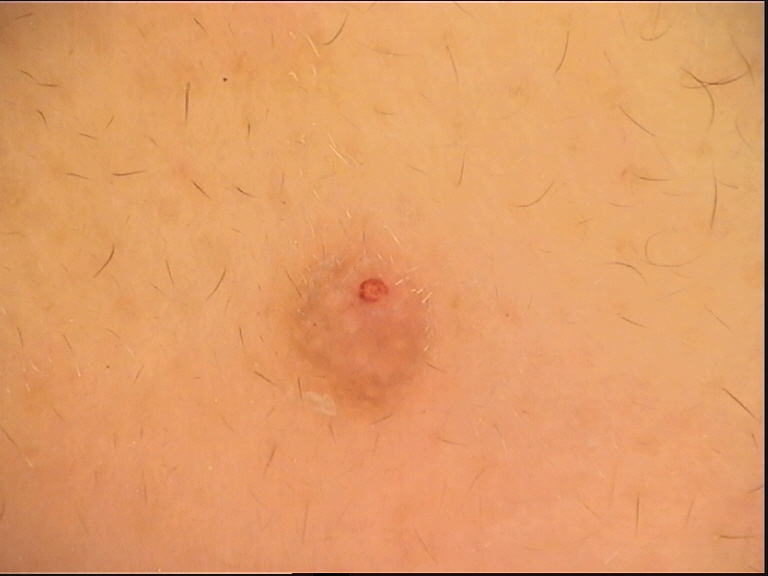class=Miescher nevus (expert consensus)